The subject is male; the head or neck is involved; this is a close-up image:
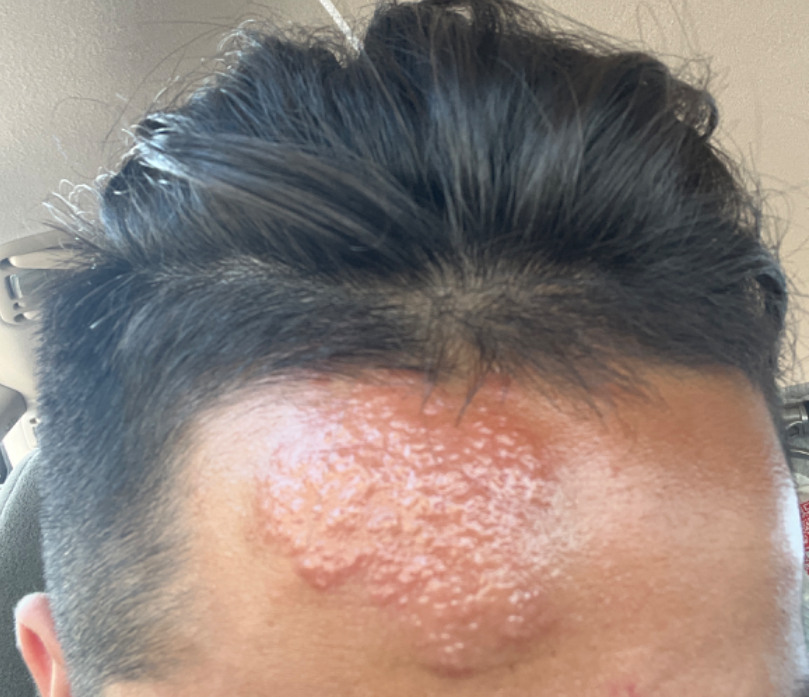<report>
  <patient_category>a rash</patient_category>
  <symptoms>none reported</symptoms>
  <duration>about one day</duration>
  <texture>fluid-filled, raised or bumpy</texture>
  <differential>
    <tied_lead>Impetigo, Granuloma faciale, Herpes Simplex, Crohn disease of skin, Localised skin infection, Granulomatous disorder of the skin and subcutaneous tissue</tied_lead>
  </differential>
</report>